A dermoscopic image of a skin lesion.
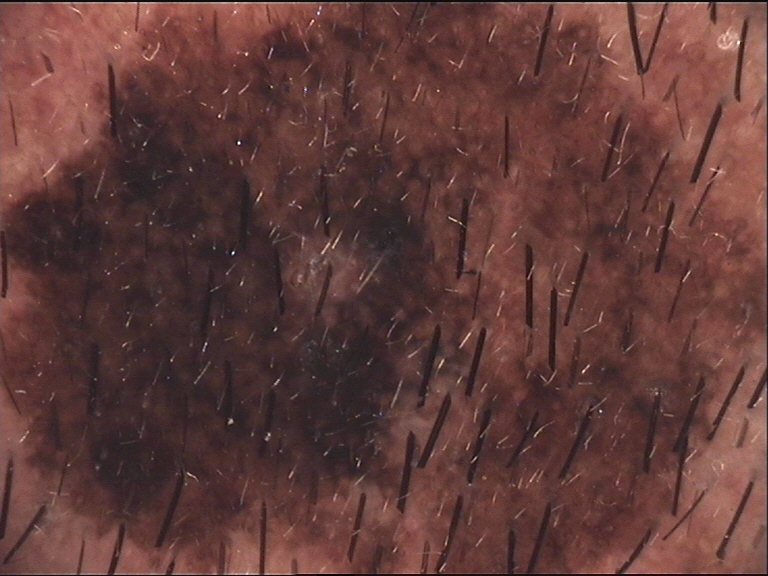Classified as a banal lesion — a congenital compound nevus.